The lesion involves the top or side of the foot. A close-up photograph: 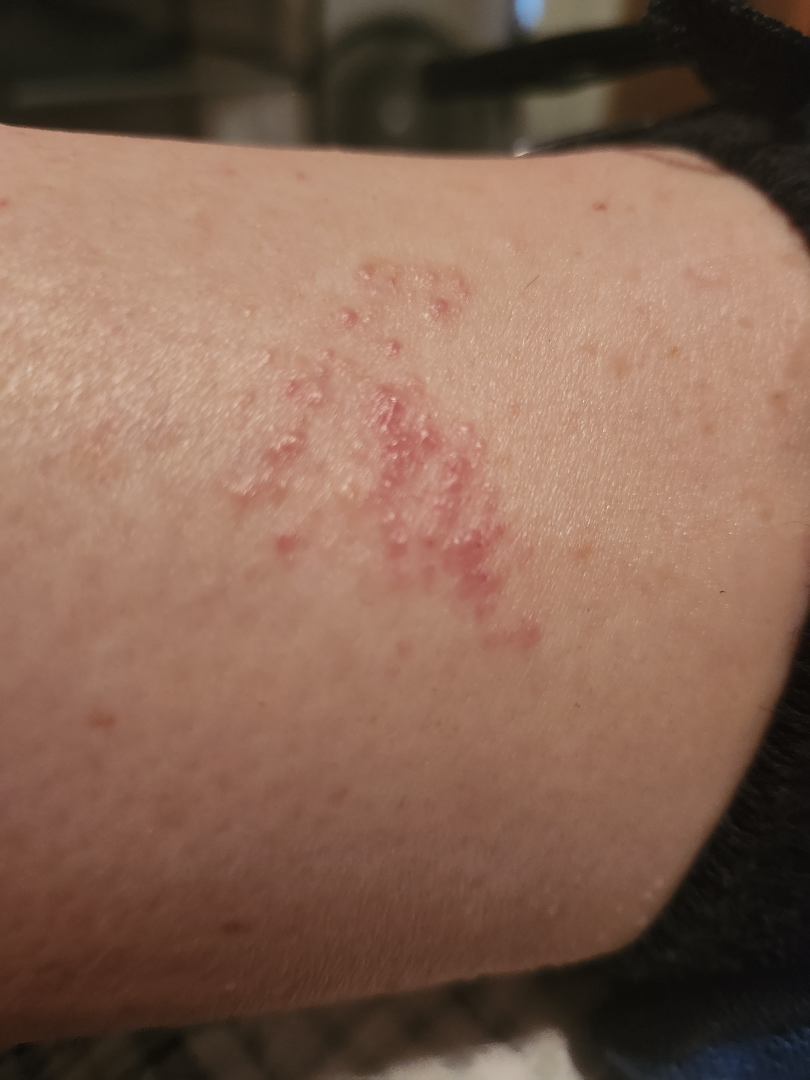Q: What was the assessment?
A: indeterminate